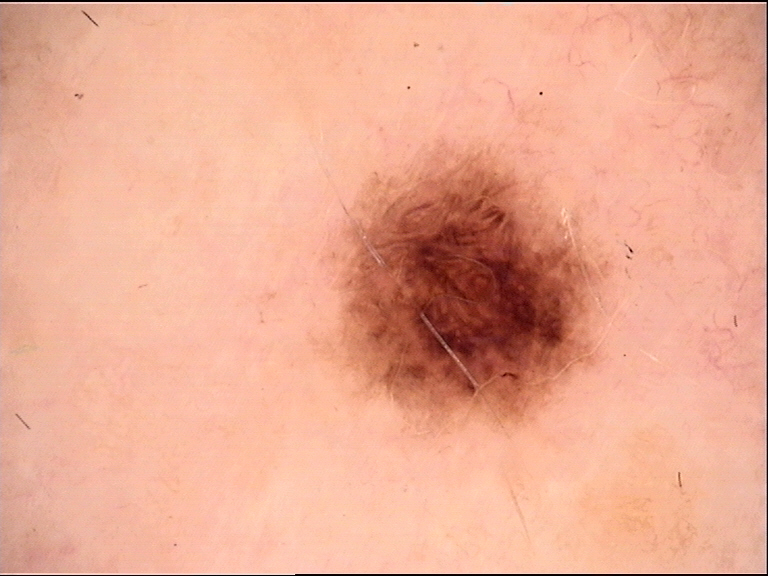A dermatoscopic image of a skin lesion. Classified as a benign lesion — a dysplastic junctional nevus.